A skin lesion imaged with a dermatoscope; a female subject, in their mid- to late 40s.
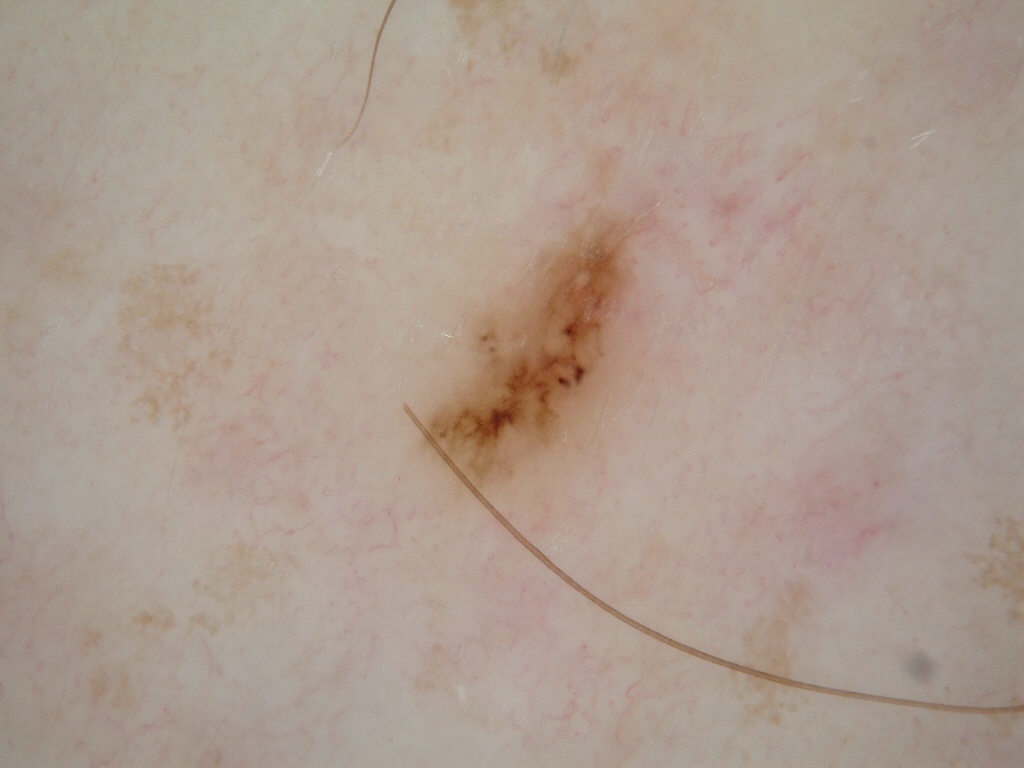Summary: As (left, top, right, bottom), the lesion is bounded by <box>395, 196, 676, 512</box>. Dermoscopic assessment notes globules. Assessment: Diagnosed as a melanocytic nevus, a benign skin lesion.